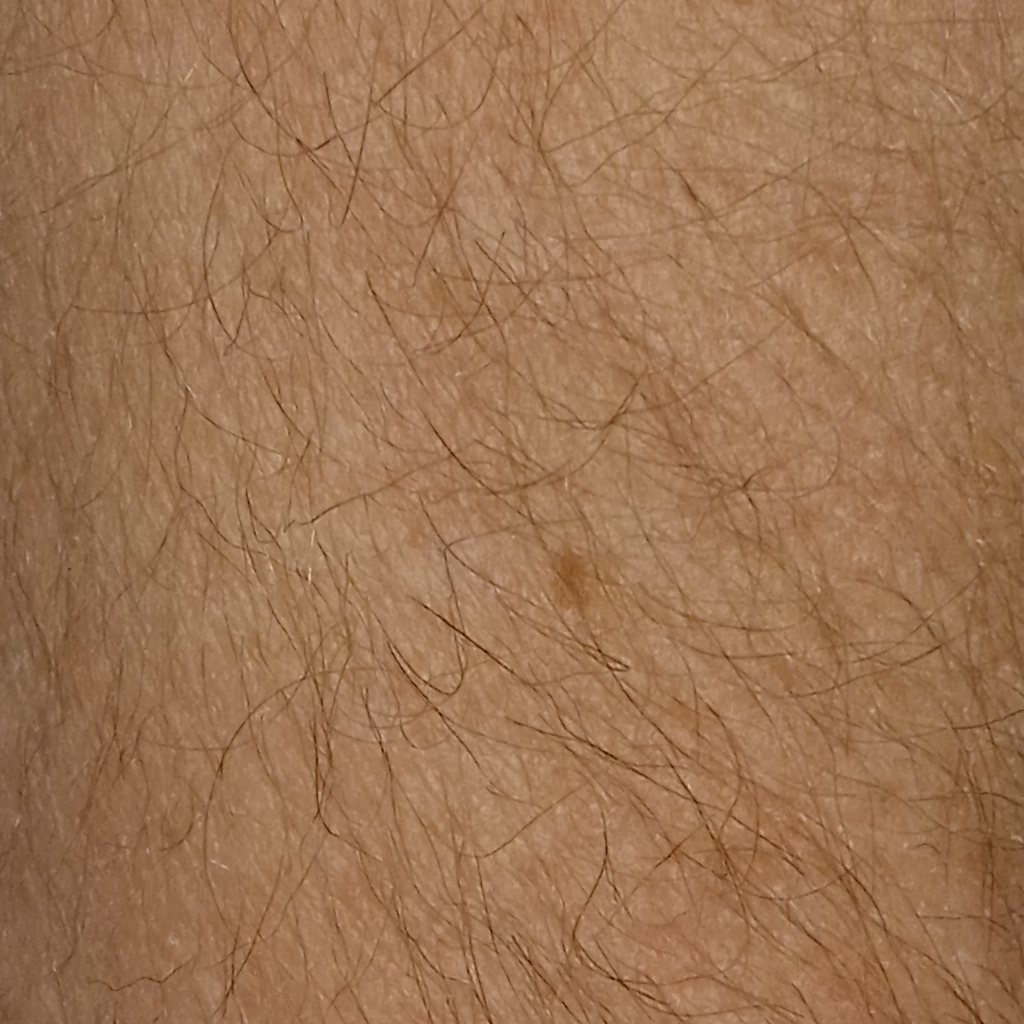Acquired for a research image collection, with no referral diagnosis. A clinical photograph showing a skin lesion. A male patient aged 66. The patient describes having few moles overall. On a questionnaire the patient reported a prior organ transplant. The patient says their skin reddens with sun exposure. The lesion involves an arm. The lesion is about 3.4 mm across. Dermatologist review favored a melanocytic nevus.